Close-up view:
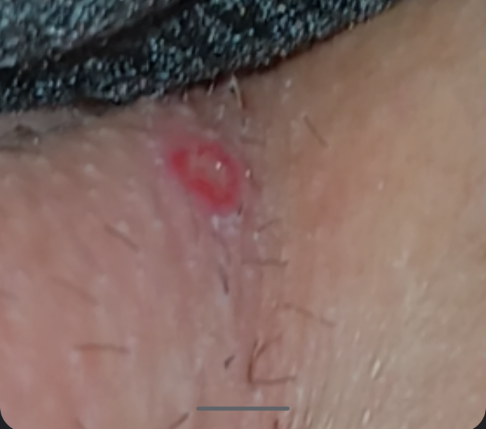Q: What was the assessment?
A: indeterminate from the photograph